A skin lesion imaged with a dermatoscope: 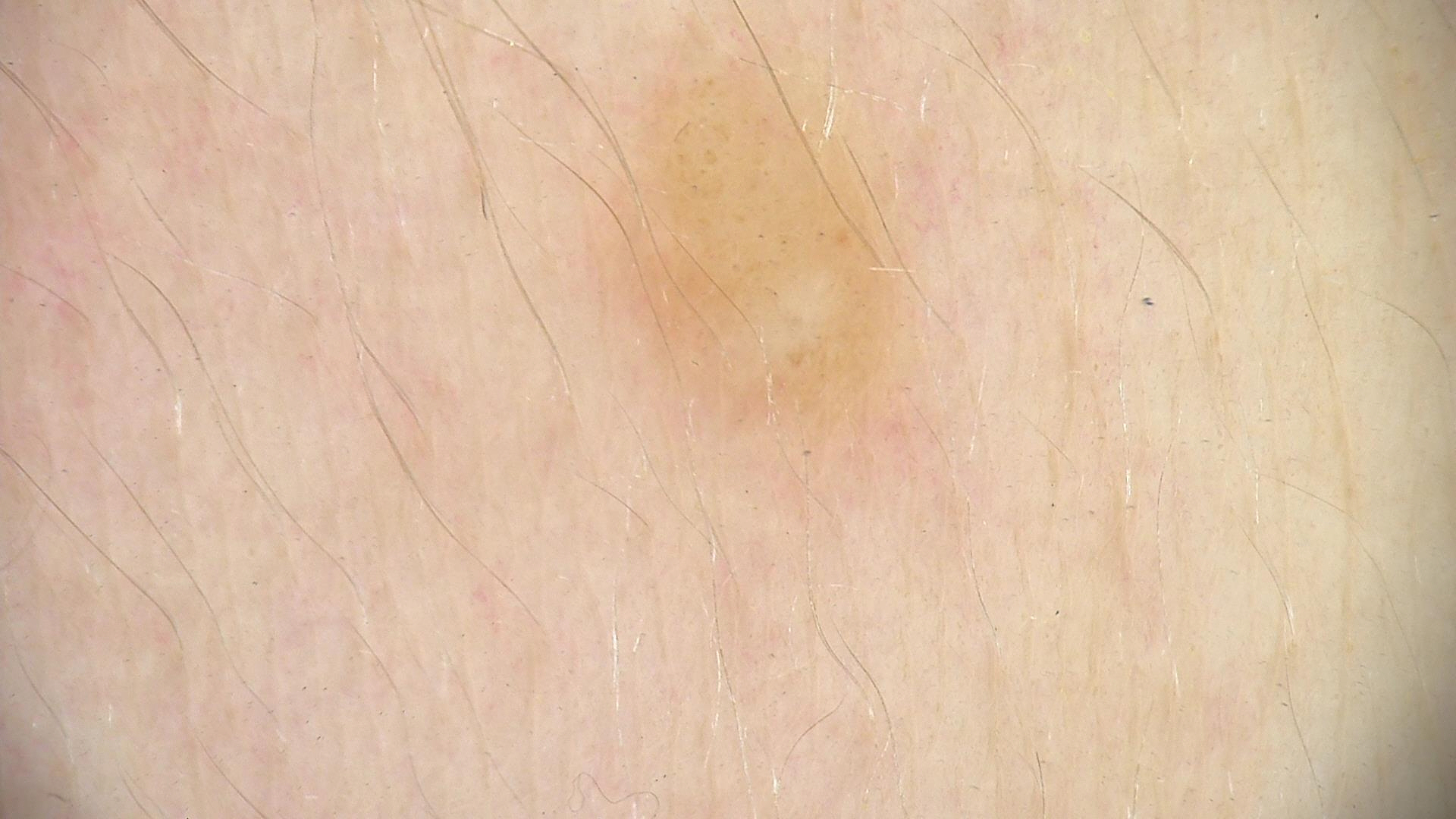The morphology is that of a banal lesion. The diagnostic label was a dermal nevus.